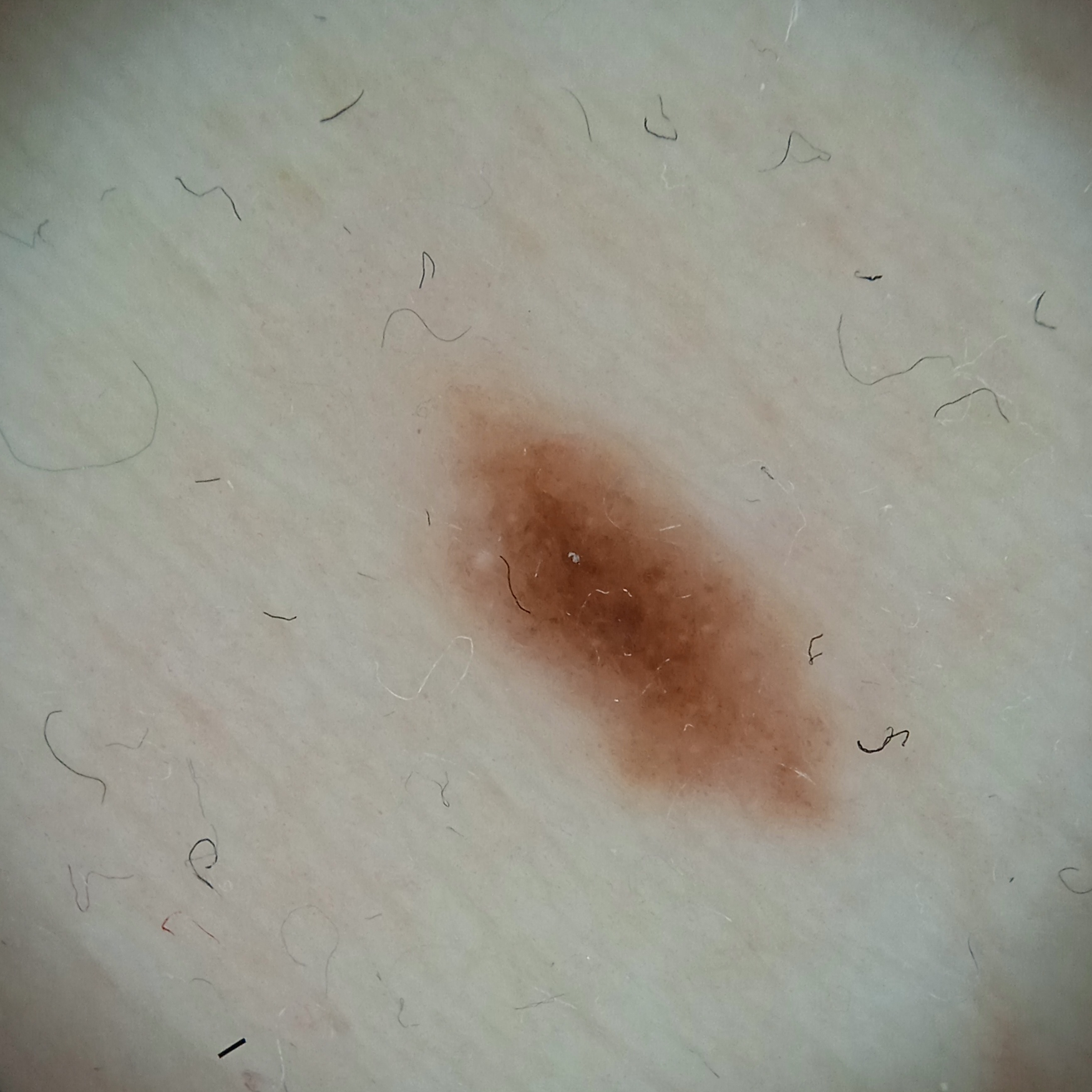Conclusion: The consensus diagnosis for this lesion was a melanocytic nevus.